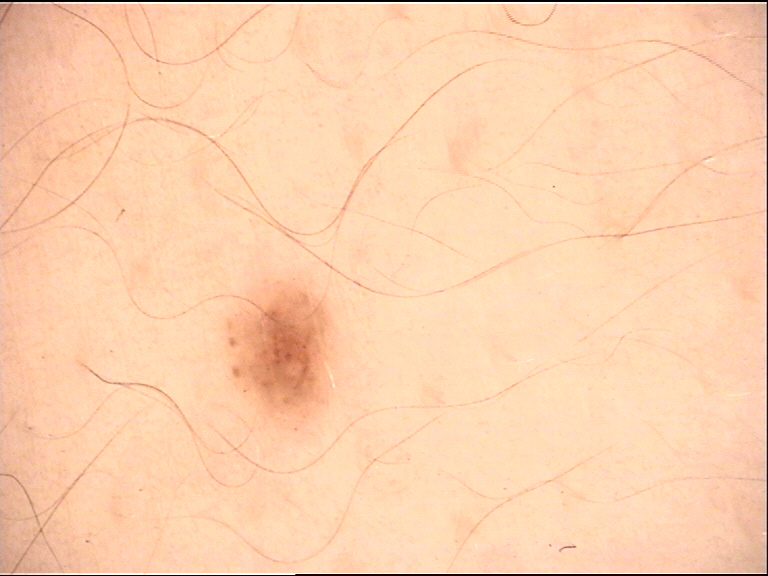{
  "image": "dermoscopy",
  "diagnosis": {
    "name": "dysplastic junctional nevus",
    "code": "jd",
    "malignancy": "benign",
    "super_class": "melanocytic",
    "confirmation": "expert consensus"
  }
}